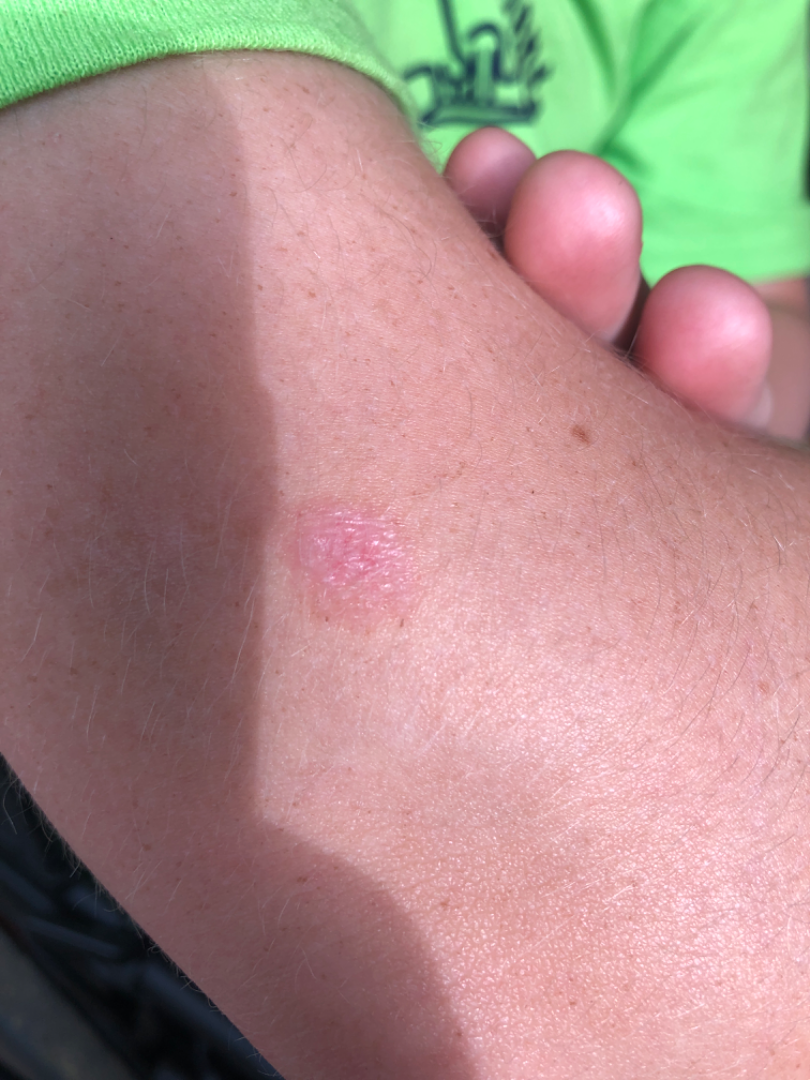Patient information:
Skin tone: Fitzpatrick skin type II; lay graders estimated a MST of 3. Close-up view.
Review:
One reviewing dermatologist: the differential includes Eczema and Basal Cell Carcinoma, with no clear leading consideration.